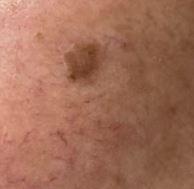Q: Patient demographics?
A: female, in their 60s
Q: What kind of image is this?
A: clinical photo (overview)
Q: Where on the body is the lesion?
A: the head or neck
Q: What was the clinical impression?
A: Seborrheic keratosis